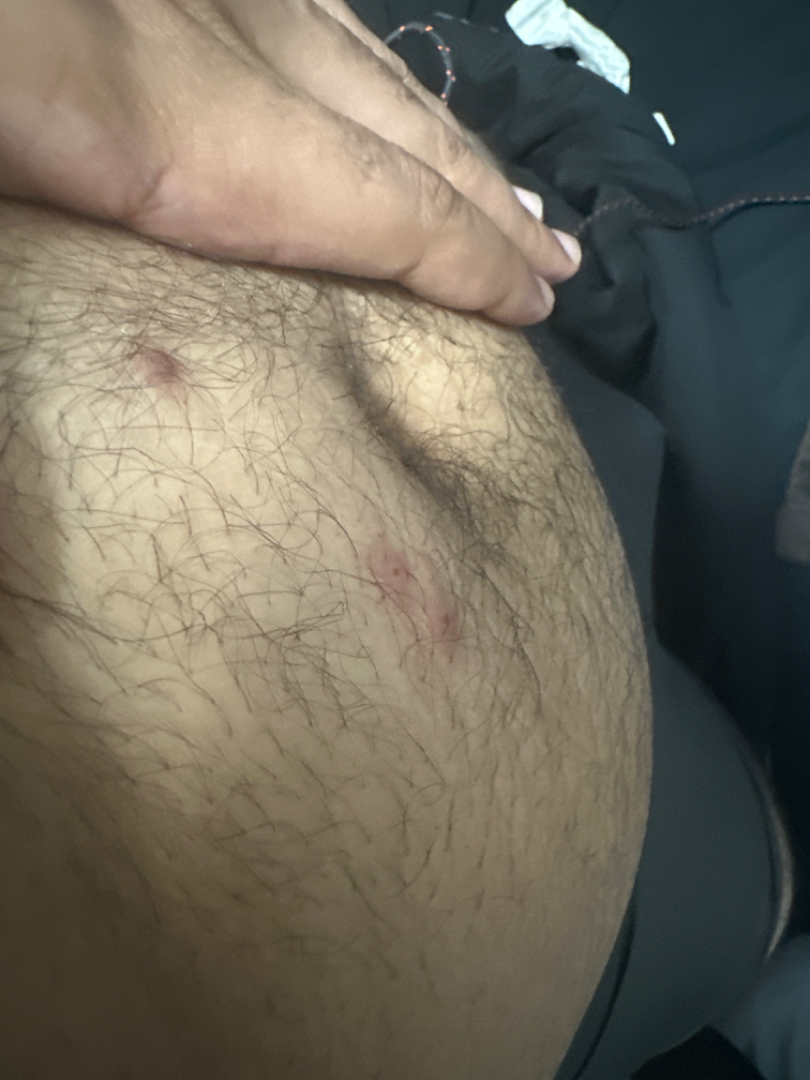assessment = indeterminate from the photograph, framing = at an angle, lesion texture = raised or bumpy and fluid-filled.